A contact-polarized dermoscopy image of a skin lesion; a male patient aged approximately 75:
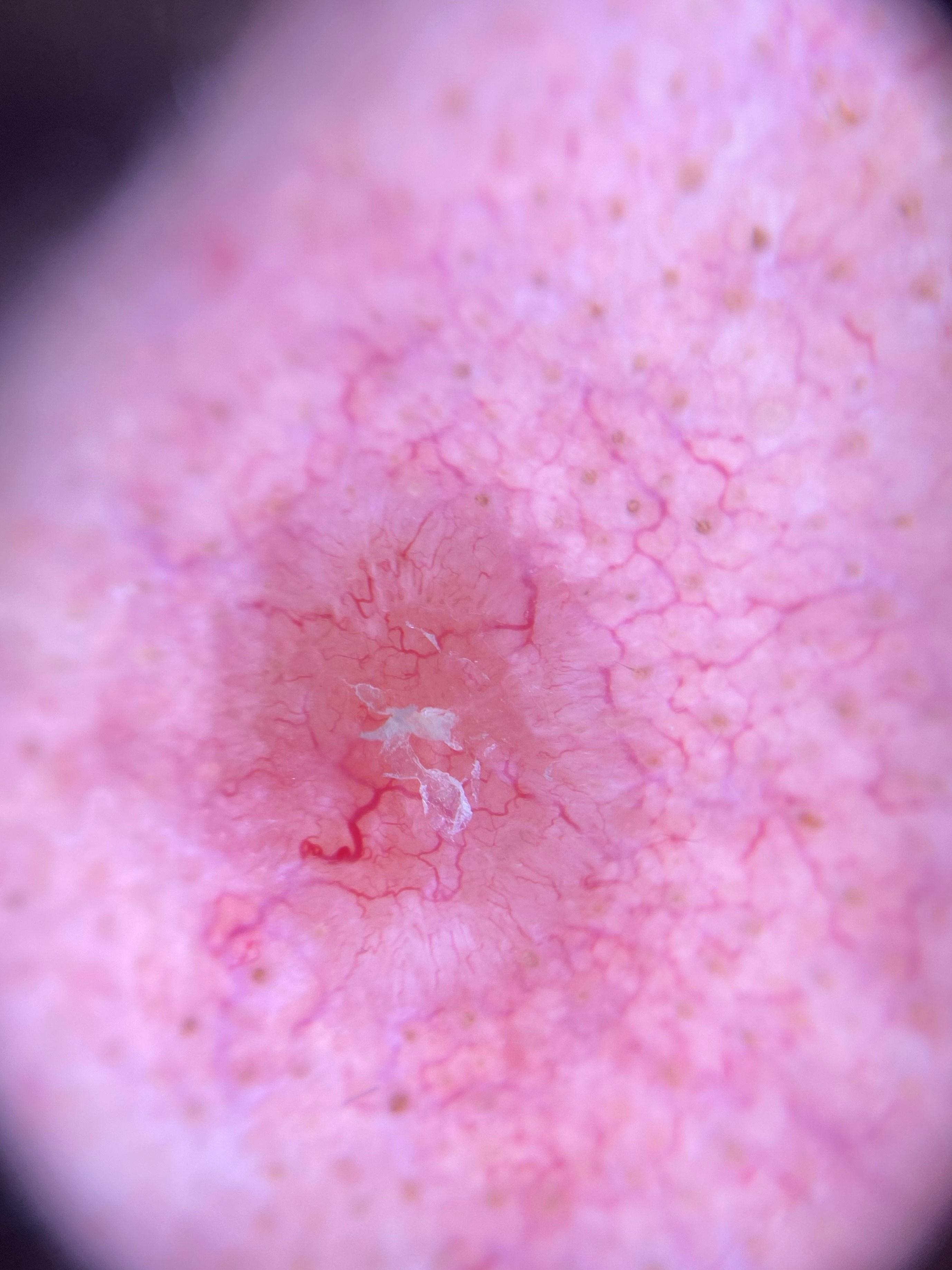Findings:
• site — the head or neck
• diagnosis — Basal cell carcinoma (biopsy-proven)